The lesion involves the leg, this is a close-up image, the patient is a female aged 18–29: 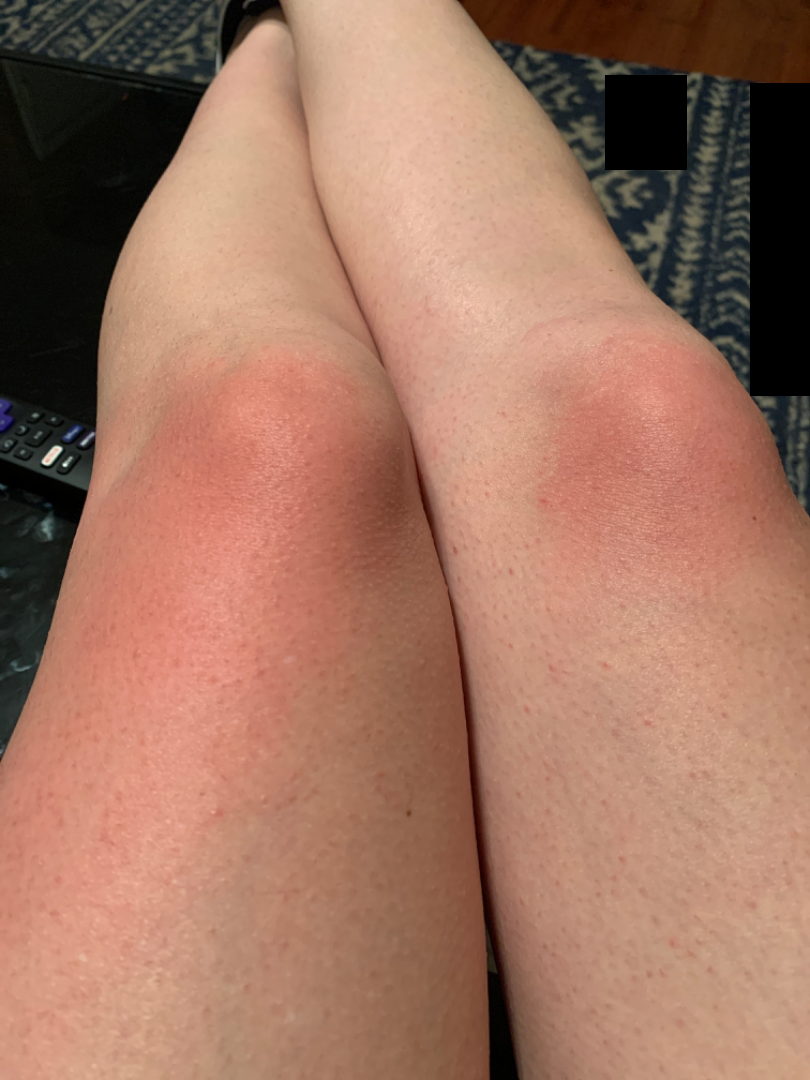Background: Self-categorized by the patient as a rash. The lesion is described as flat. Reported duration is about one day. The patient notes burning. Findings: The reviewing dermatologist's impression was: Photodermatitis (most likely).